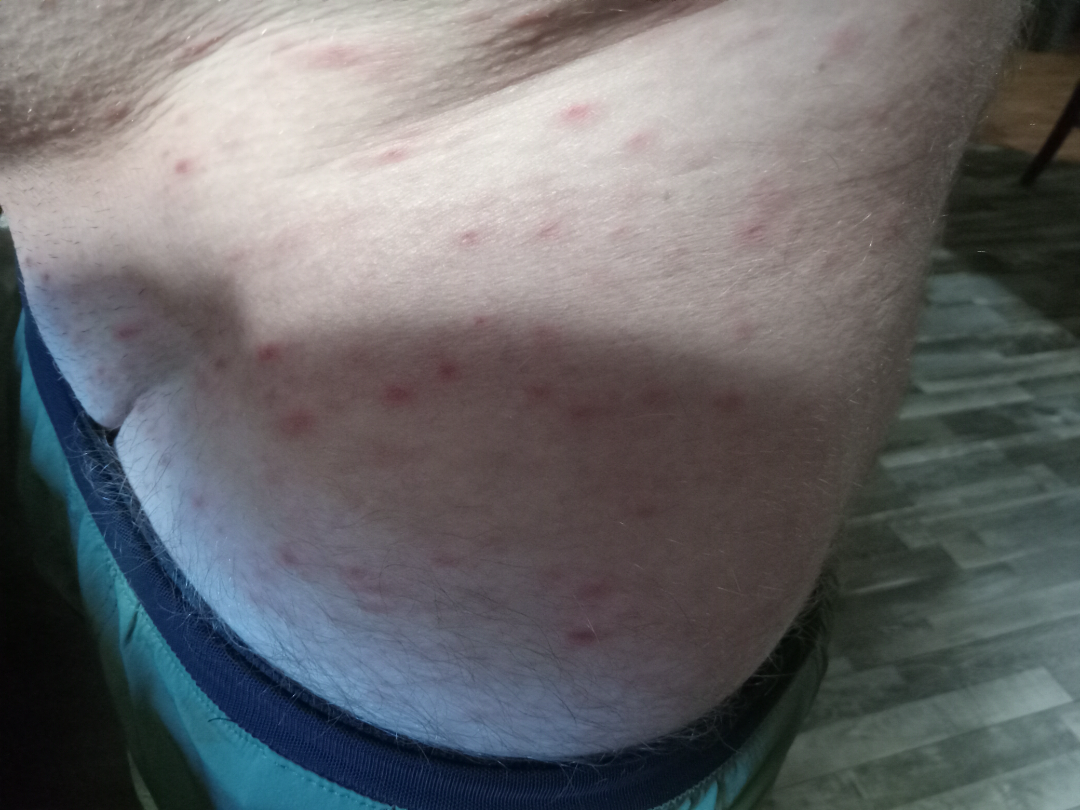<case>
<shot_type>close-up</shot_type>
</case>